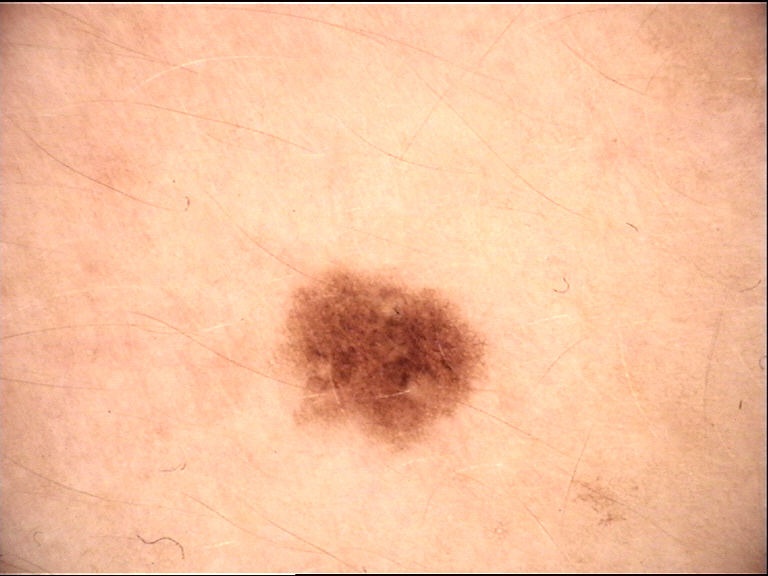Findings:
• class — junctional nevus (expert consensus)